A skin lesion imaged with a dermatoscope.
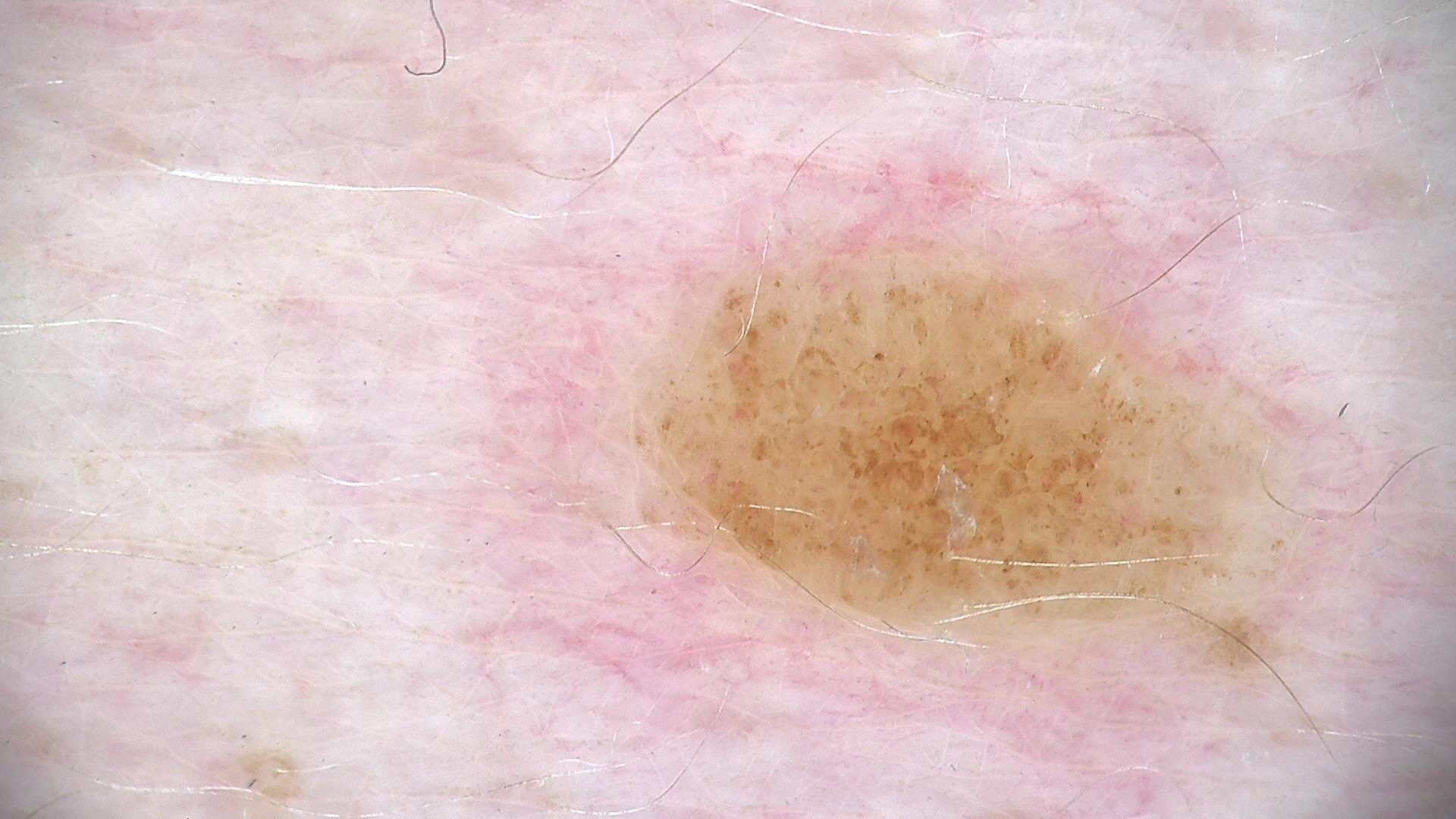{
  "lesion_type": {
    "main_class": "banal",
    "pattern": "compound"
  },
  "diagnosis": {
    "name": "compound nevus",
    "code": "cb",
    "malignancy": "benign",
    "super_class": "melanocytic",
    "confirmation": "expert consensus"
  }
}